A dermoscopic view of a skin lesion:
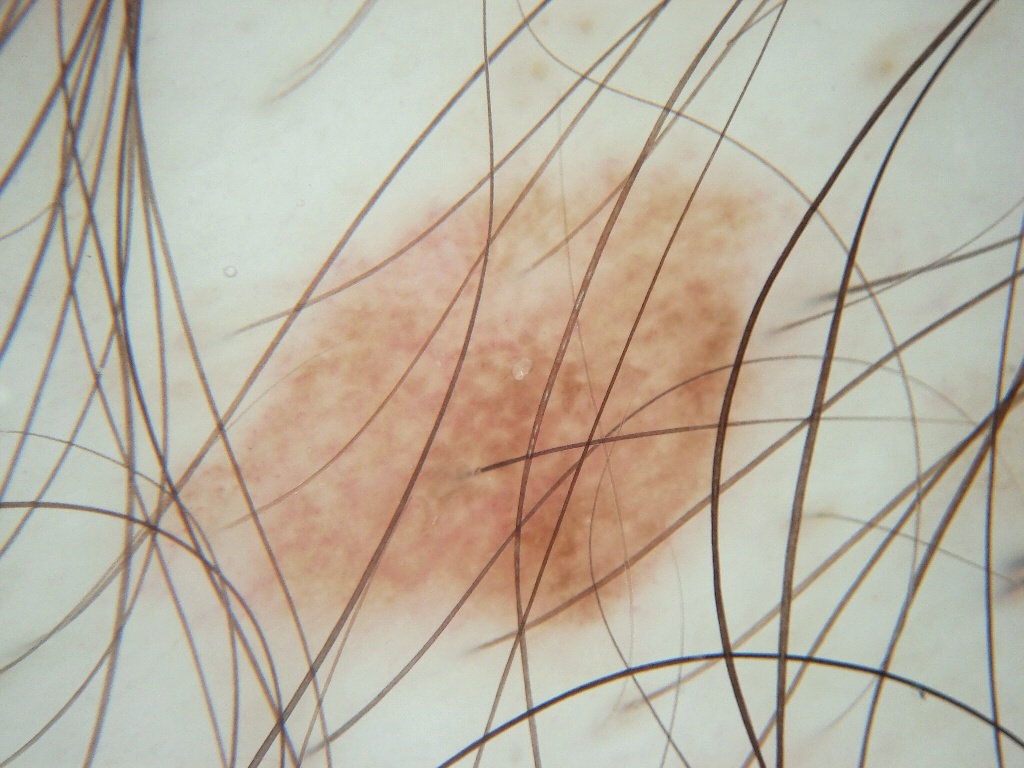Summary:
A prominent lesion filling much of the field. The lesion's extent is 137 139 795 650.
Impression:
The lesion was assessed as a benign lesion.